Female contributor, age 40–49. This image was taken at a distance. The affected area is the back of the hand and arm:
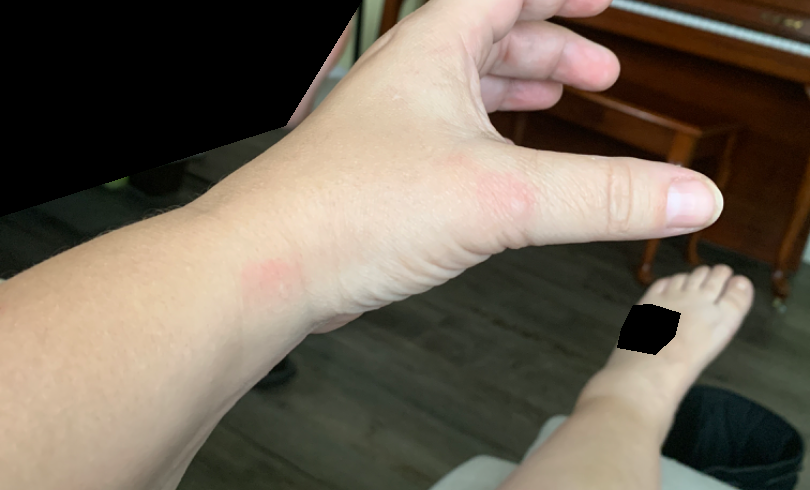The skin findings could not be characterized from the image. Present for about one day. The lesion is described as raised or bumpy.